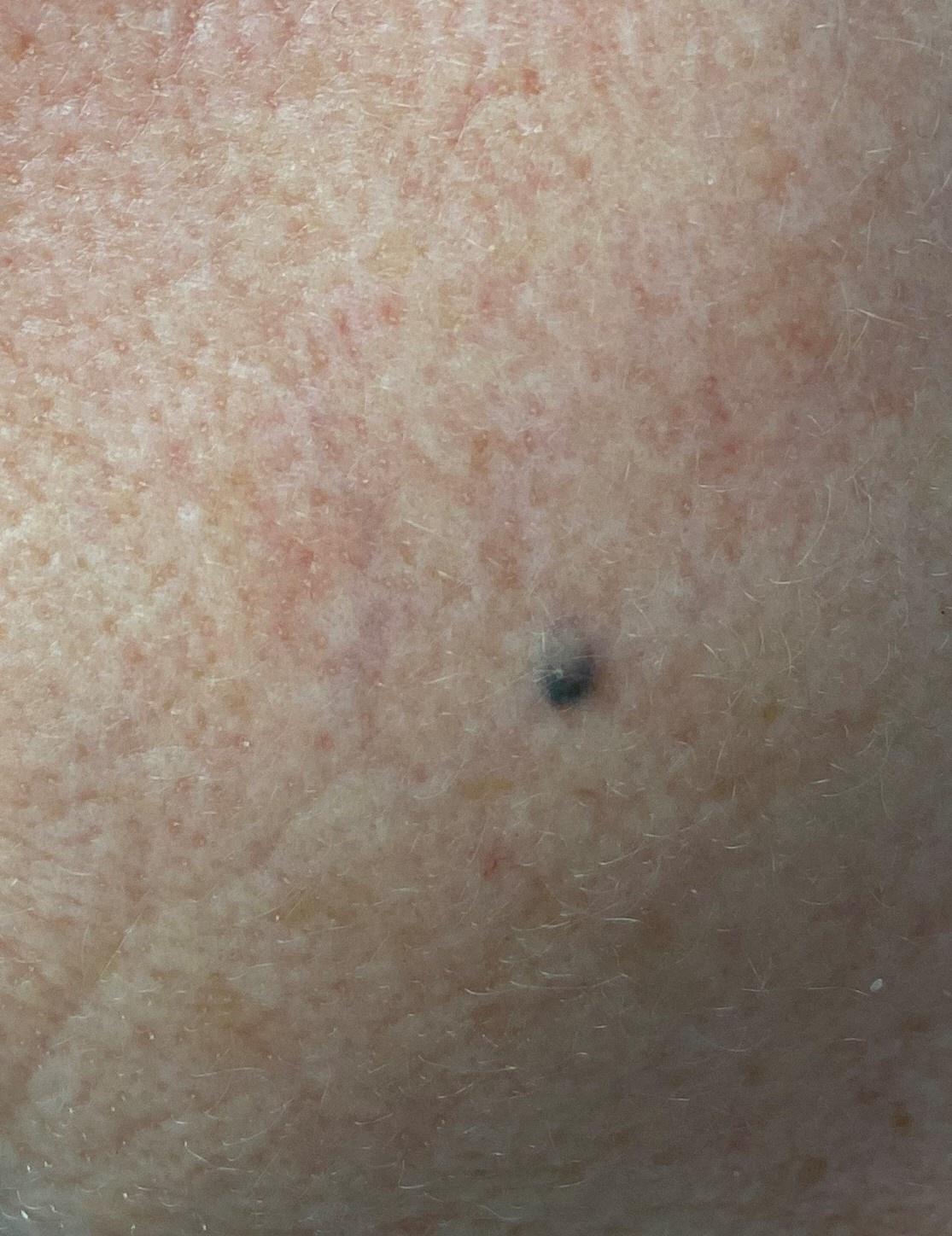{"patient": {"age_approx": 70, "sex": "female"}, "image": "clinical photograph", "lesion_location": {"region": "the head or neck"}, "diagnosis": {"name": "Nevus", "malignancy": "benign", "confirmation": "expert clinical impression", "lineage": "melanocytic"}}